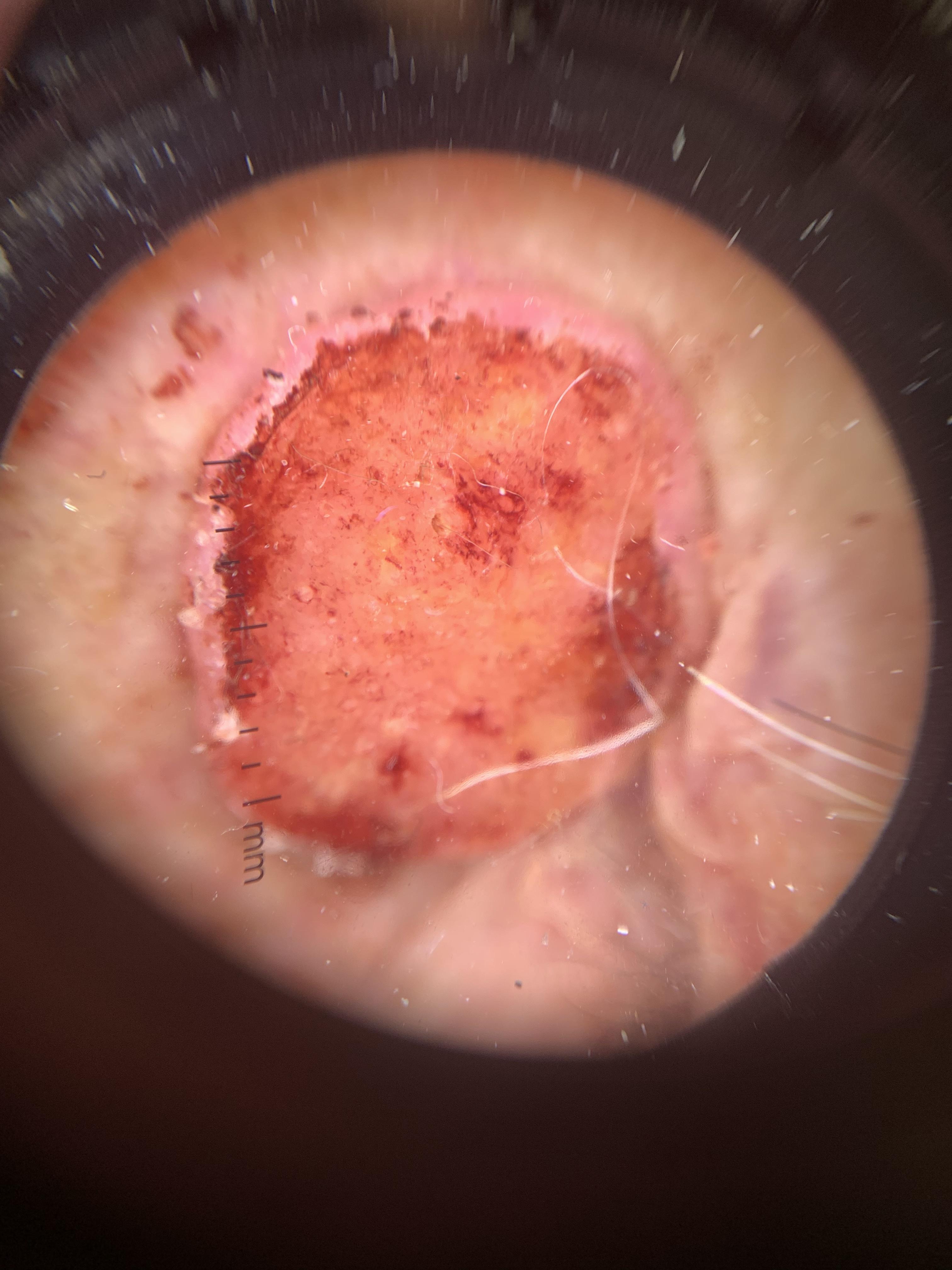Findings: A female subject about 60 years old. Dermoscopy of a skin lesion. Recorded as skin type II. The lesion is located on the head or neck. Conclusion: Confirmed on histopathology as a squamous cell carcinoma.